On a questionnaire the patient reported no family history of skin cancer · imaged for a research study, with no referral diagnosis recorded · a female subject aged 59 · the patient says their skin reddens with sun exposure · dermoscopy of a skin lesion · a moderate number of moles by the patient's own estimate.
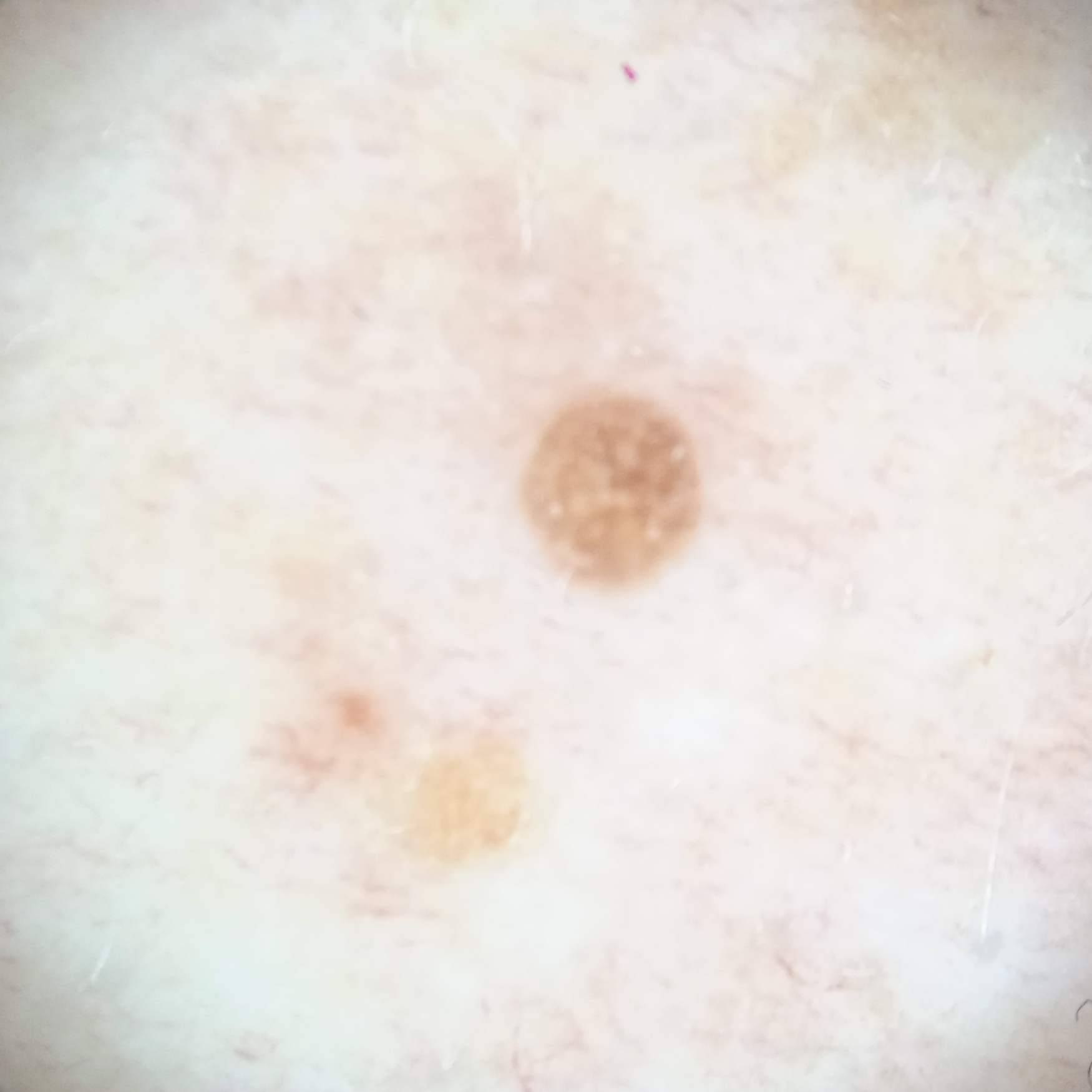location: the torso; diameter: 2.2 mm; diagnostic label: seborrheic keratosis (dermatologist consensus).